A dermoscopic close-up of a skin lesion.
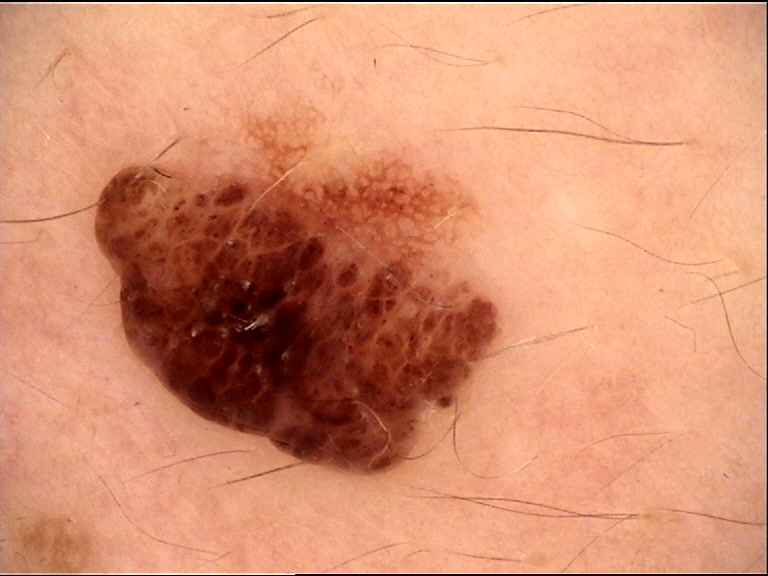• class · compound nevus (expert consensus)